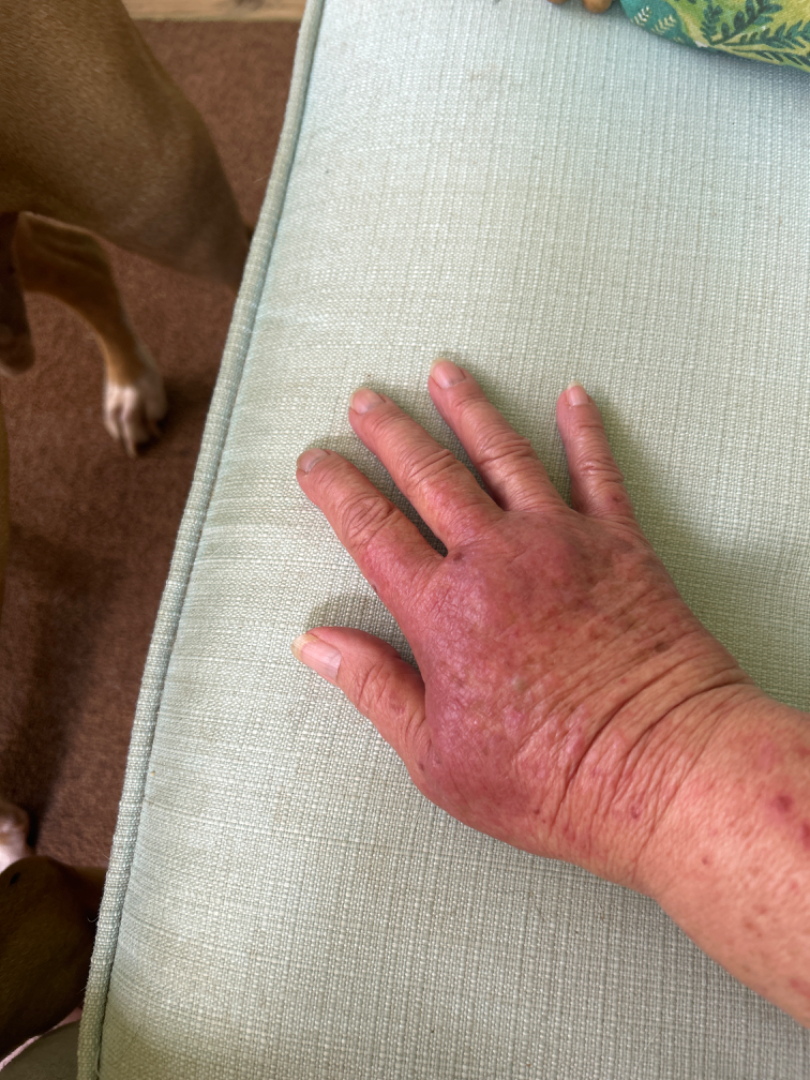assessment: could not be assessed
patient: female, age 60–69
anatomic site: back of the hand
view: close-up
skin tone: Fitzpatrick skin type III
patient describes the issue as: a rash
texture: raised or bumpy
reported symptoms: itching, bothersome appearance and burning